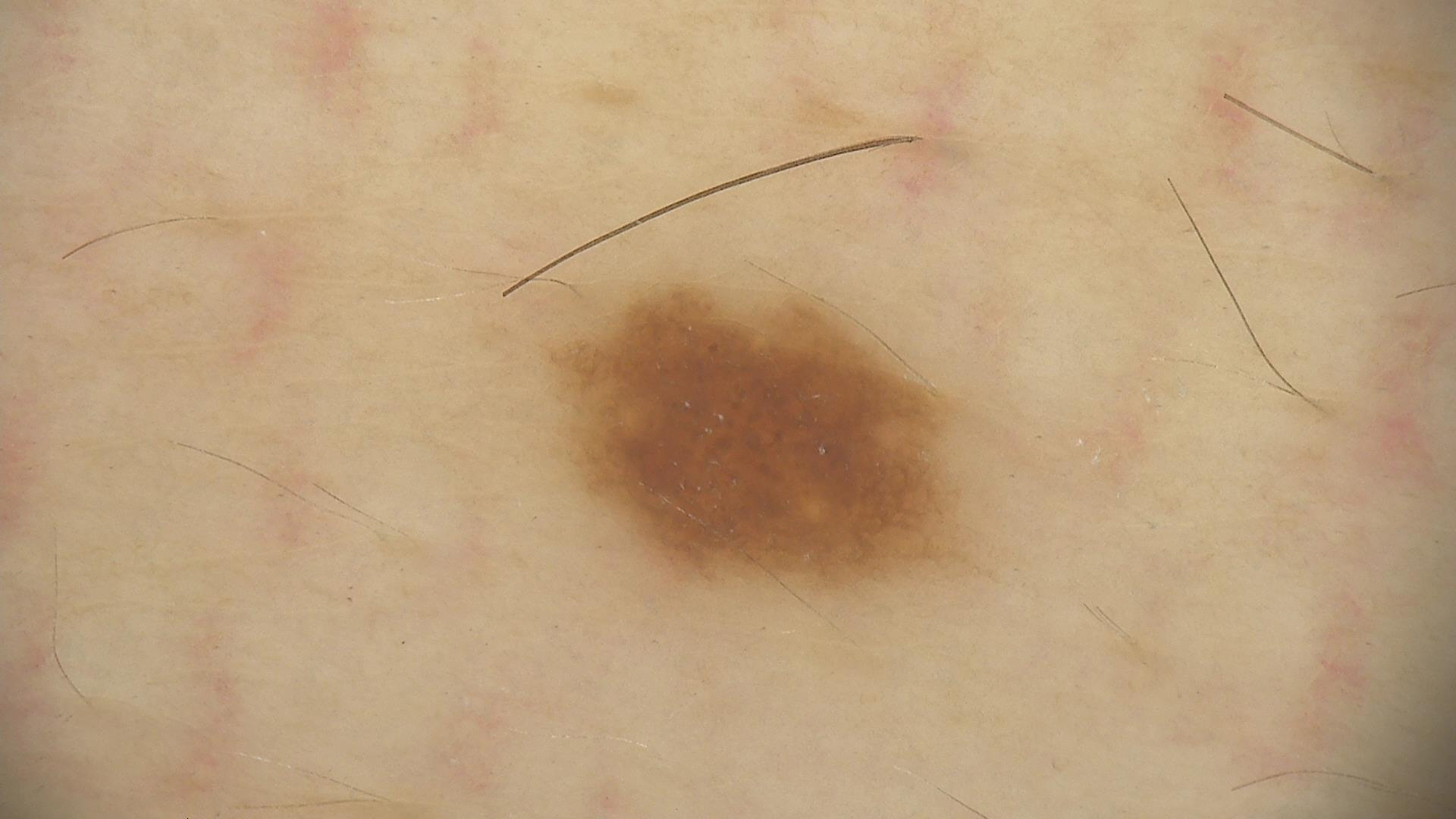Impression:
Consistent with a dysplastic junctional nevus.